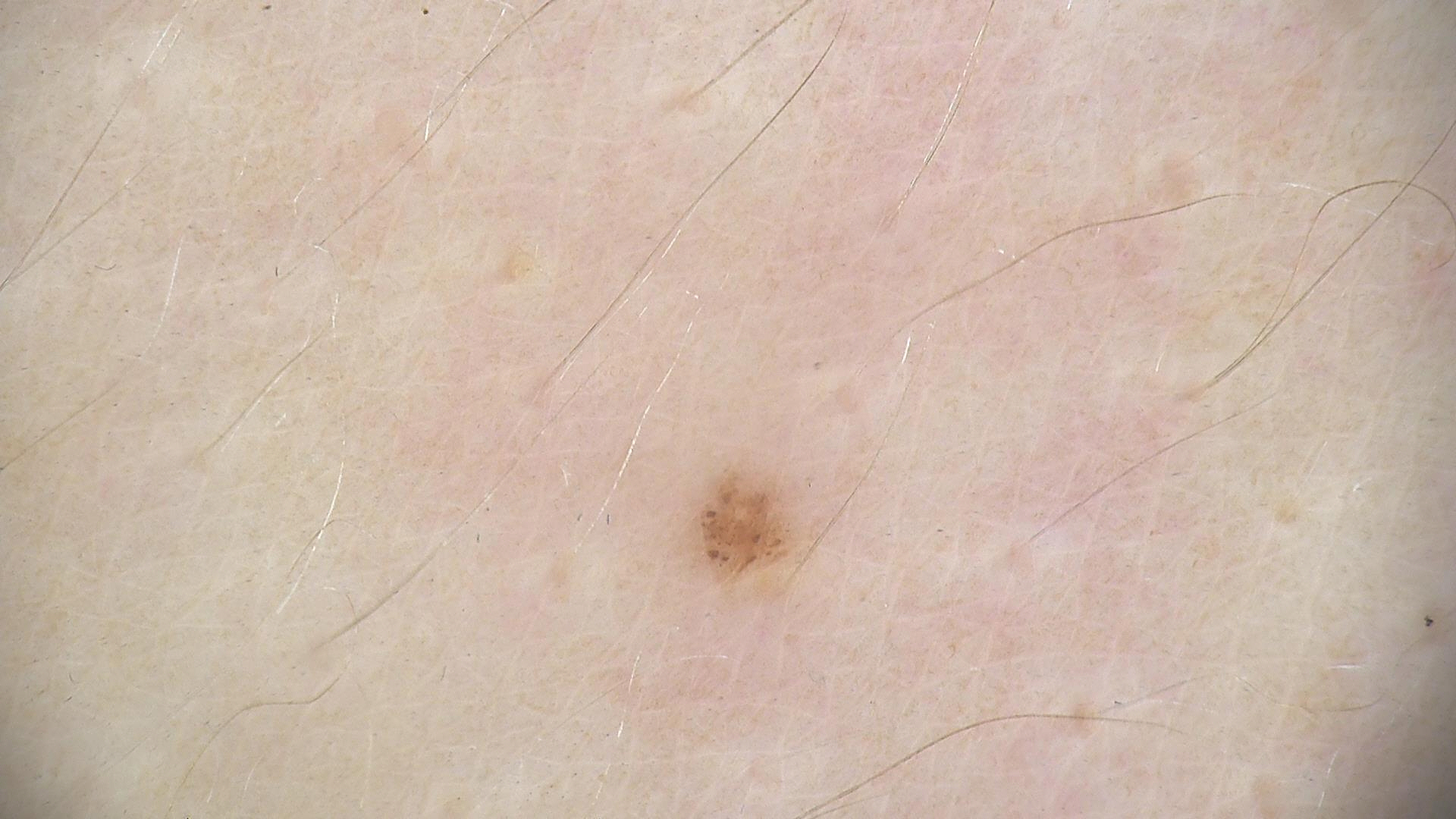Case:
* imaging · dermoscopy
* class · dysplastic junctional nevus (expert consensus)